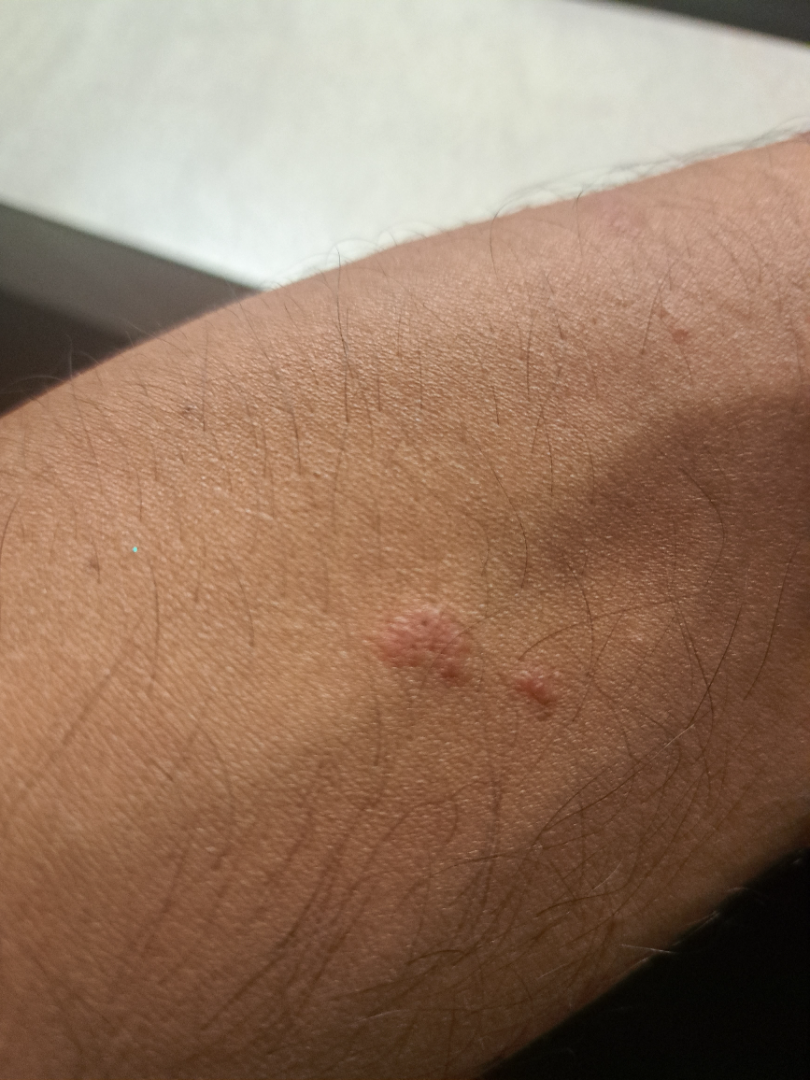| key | value |
|---|---|
| assessment | indeterminate |
| photo taken | close-up |
| described texture | fluid-filled and raised or bumpy |
| anatomic site | head or neck, leg, arm and back of the hand |
| symptoms | itching |
| constitutional symptoms | none reported |
| skin tone | FST IV; lay graders estimated MST 4 or 6 |
| patient's own categorization | a rash |